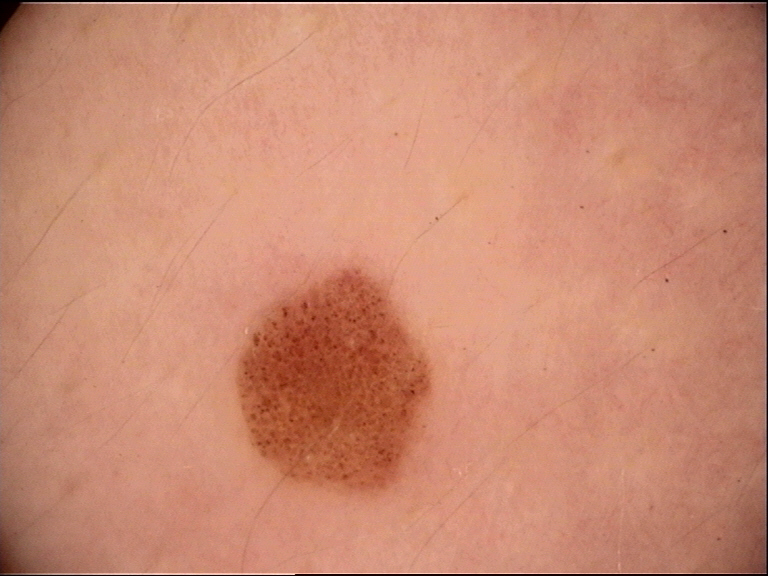Diagnosed as a dysplastic junctional nevus.